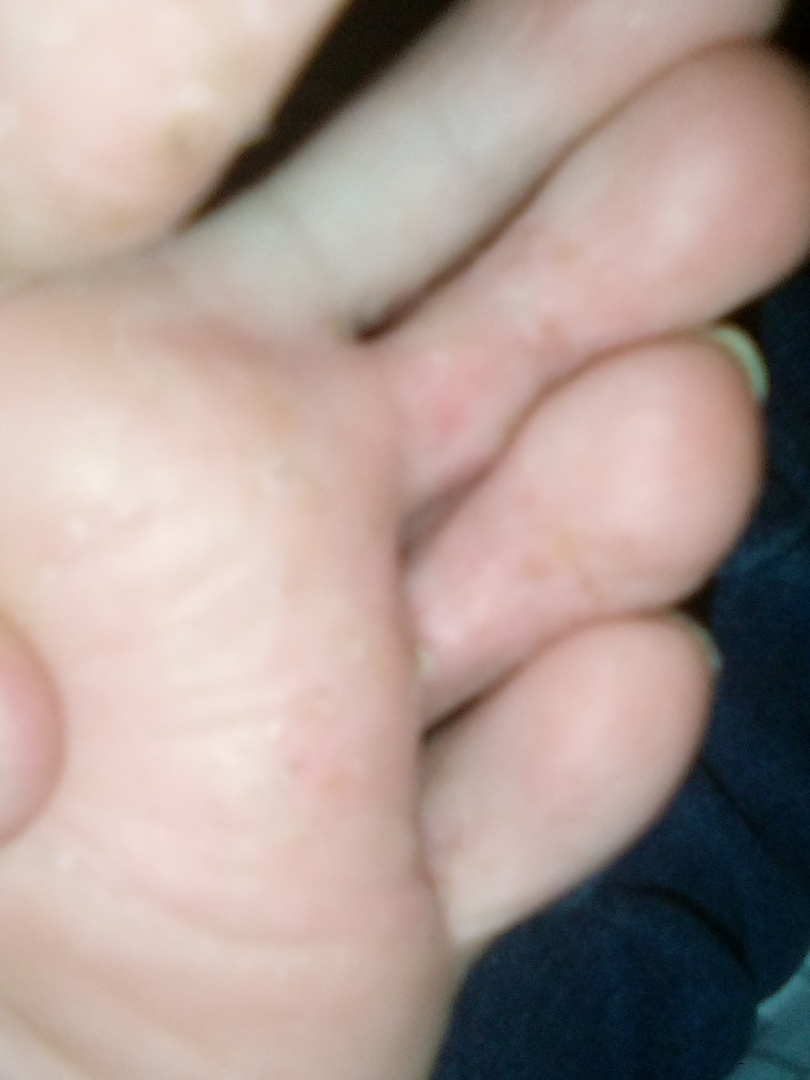anatomic site — top or side of the foot
associated systemic symptoms — none reported
texture — rough or flaky and raised or bumpy
view — close-up
lesion symptoms — pain, itching and burning
dermatologist impression — Tinea (most likely); Chilblain (possible); Eczema (possible)